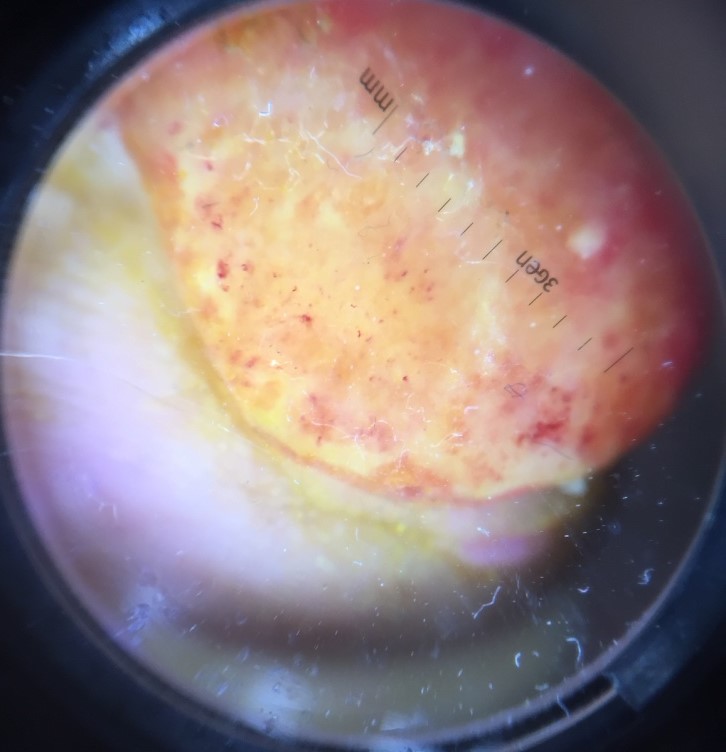Case:
A dermatoscopic image of a skin lesion.
Conclusion:
Histopathology confirmed an acral nodular melanoma.